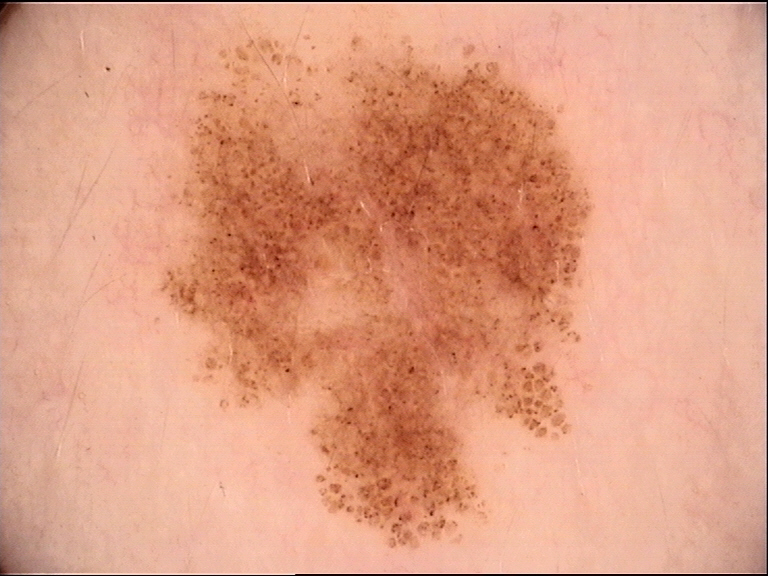Dermoscopy of a skin lesion. The diagnostic label was a dysplastic junctional nevus.